A dermoscopy image of a single skin lesion:
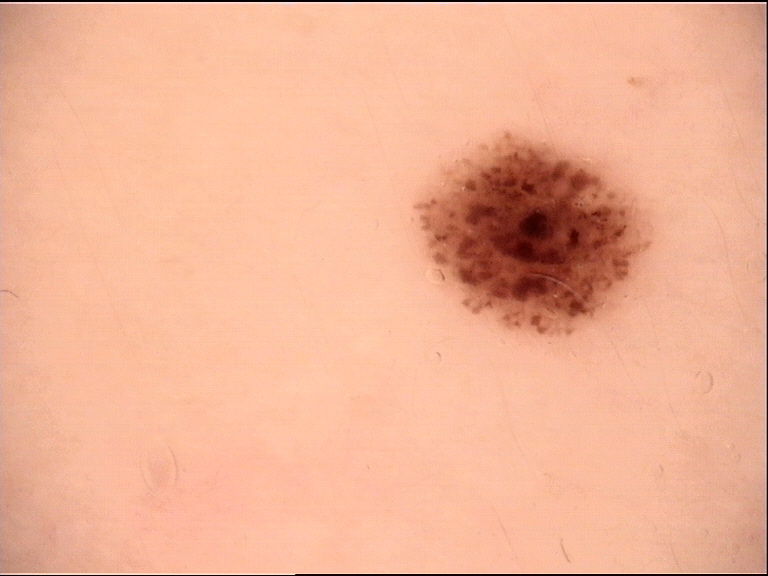Q: What is this lesion?
A: dysplastic compound nevus (expert consensus)